The patient notes the lesion is raised or bumpy · the photograph was taken at an angle · the patient is a female aged 40–49 · the patient considered this a rash · the patient notes burning, itching and enlargement · the lesion involves the arm, front of the torso and leg · no constitutional symptoms were reported — 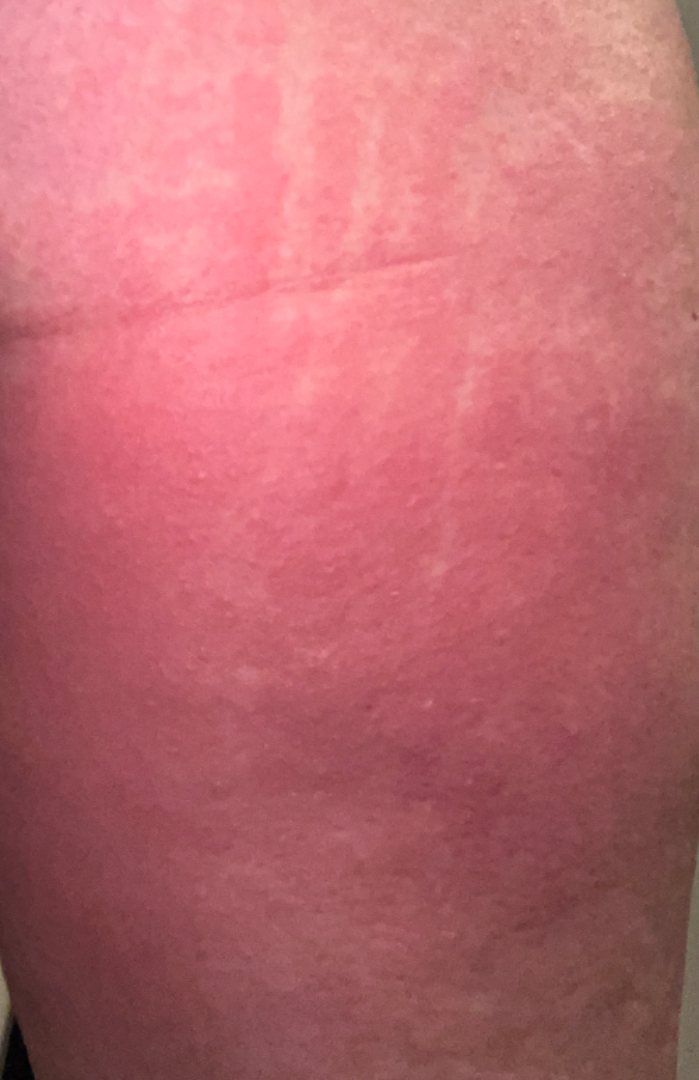• differential: the impression is Urticaria